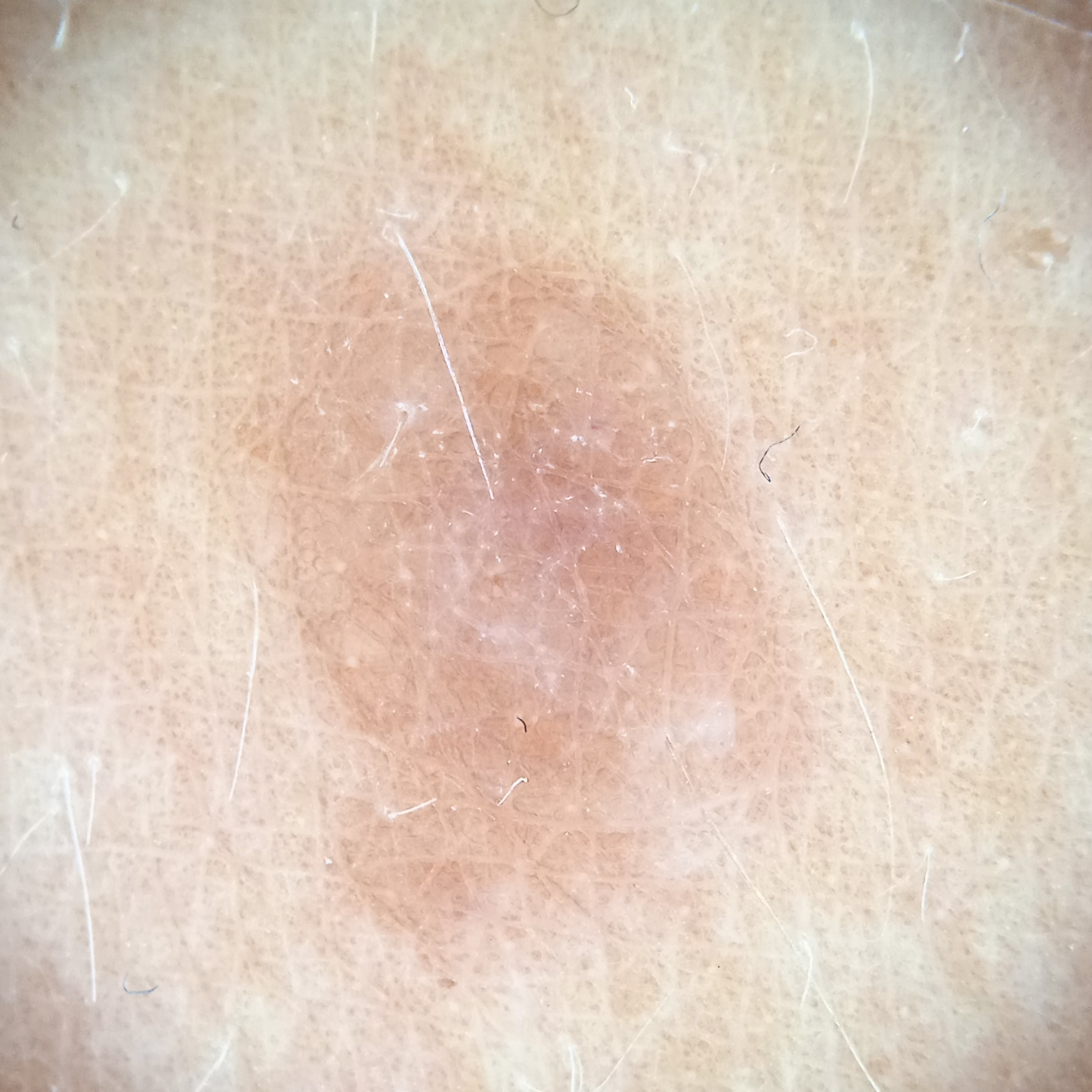The lesion was left diagnostically undetermined on review. Clinical context: A dermoscopic image of a skin lesion. A female patient aged 47. The patient says their skin tans without first burning. Located on an arm. The lesion is about 8.1 mm across.